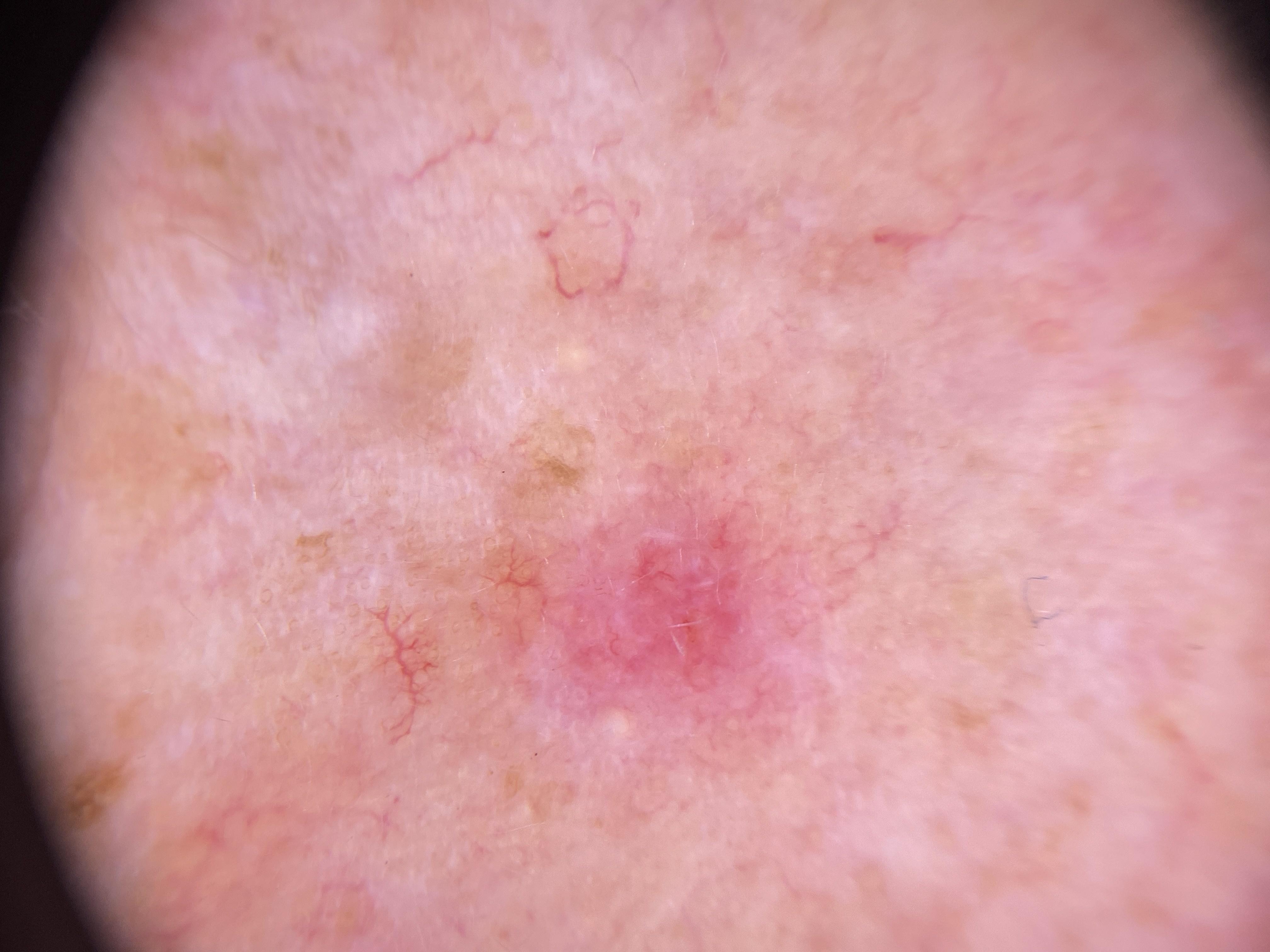Fitzpatrick: II | image: contact-polarized dermoscopy | subject: female, aged approximately 65 | location: the head or neck | diagnosis: Basal cell carcinoma (biopsy-proven).